A dermoscopy image of a single skin lesion:
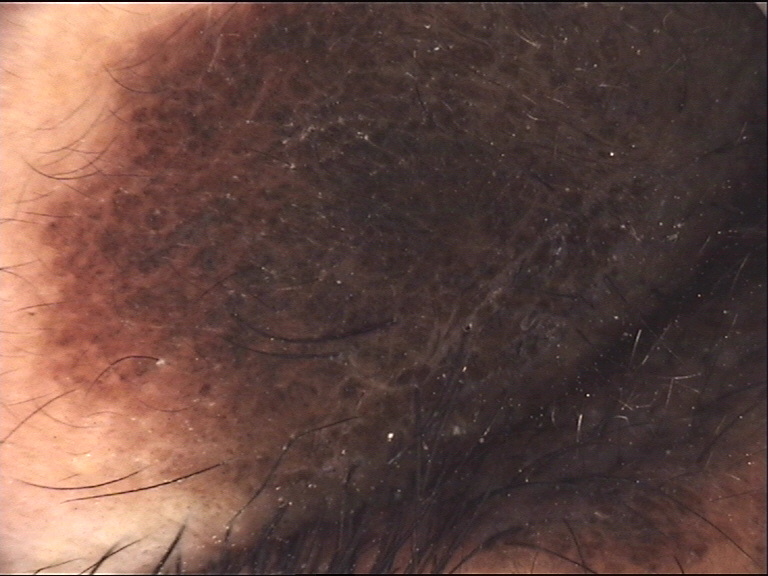assessment = congenital compound nevus (expert consensus)